The lesion involves the arm; the lesion is associated with itching; the photograph was taken at an angle; the patient considered this skin that appeared healthy to them; the patient reported no systemic symptoms; the condition has been present for about one day; the patient notes the lesion is raised or bumpy: 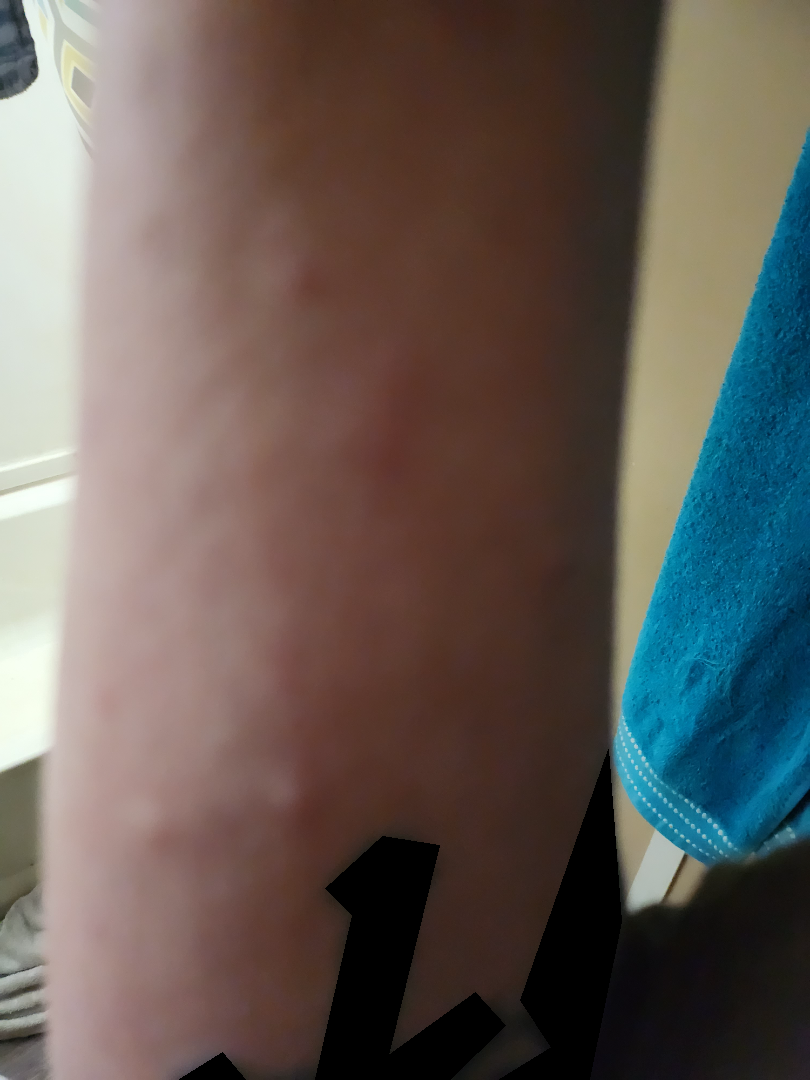No differential diagnosis could be assigned on photographic review.